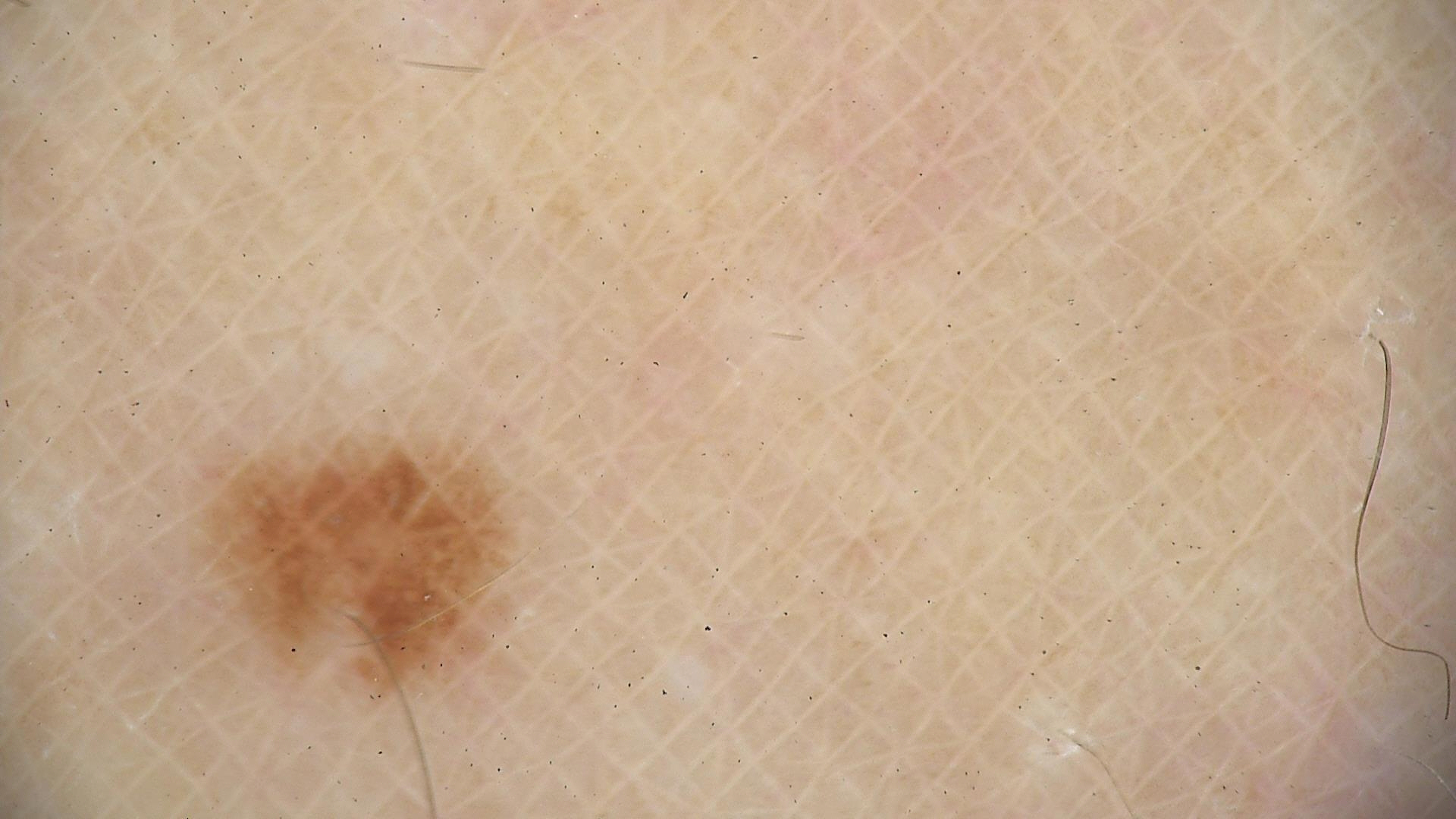Q: What is the diagnosis?
A: dysplastic junctional nevus (expert consensus)